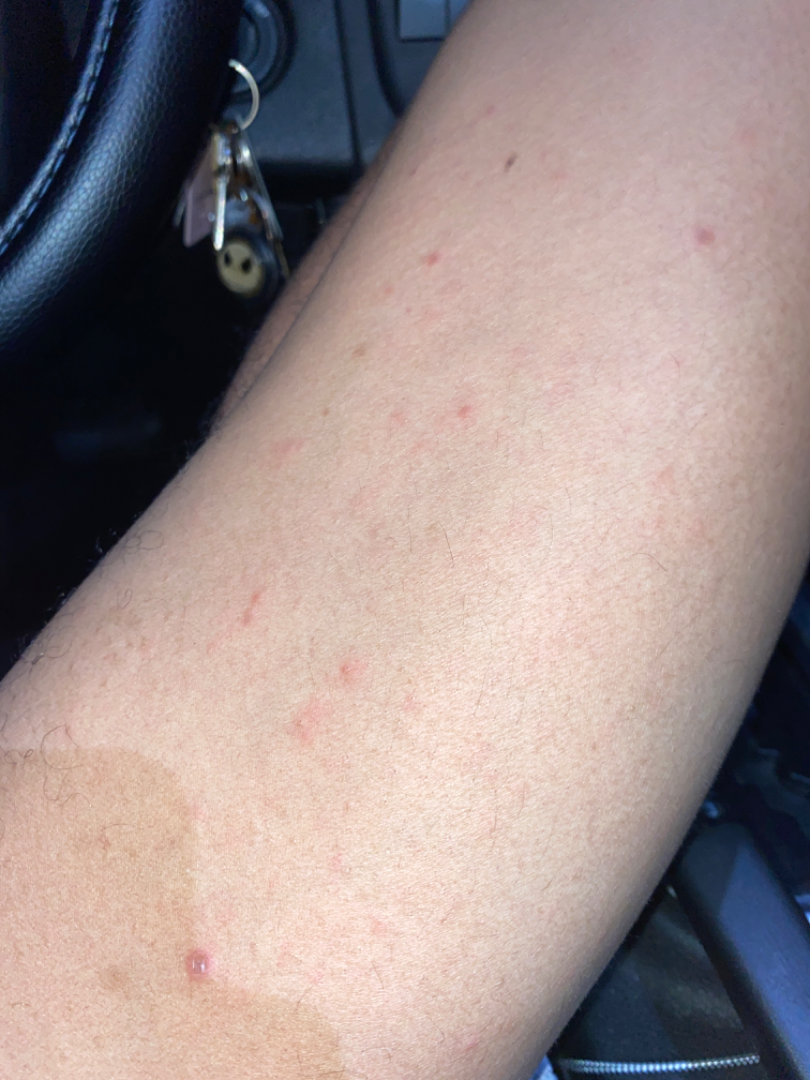This image was taken at an angle.
Texture is reported as raised or bumpy.
No relevant systemic symptoms.
Located on the leg.
Symptoms reported: bothersome appearance.
The patient is 18–29, male.
The patient described the issue as a rash.
Favoring Psoriasis; possibly Lichen planus/lichenoid eruption; an alternative is Syphilis; a remote consideration is Drug Rash; less likely is Eczema.